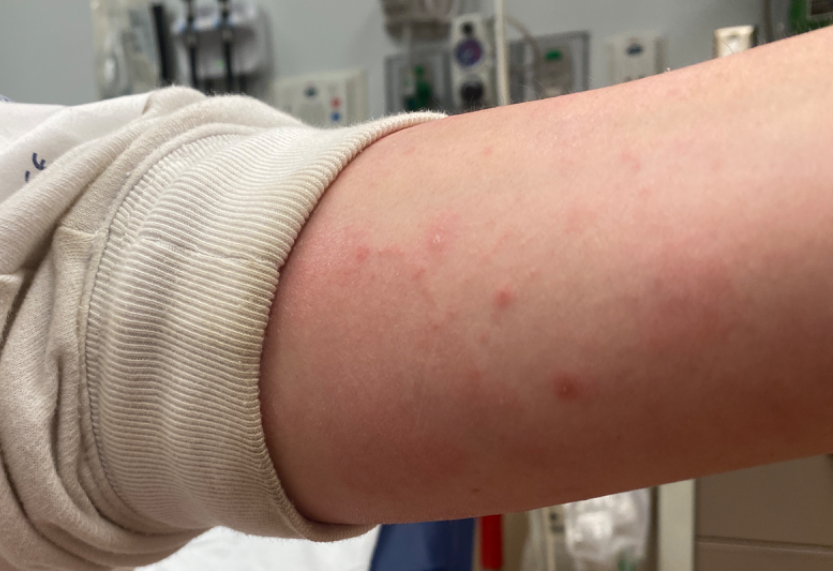Diagnostic features were not clearly distinguishable in this photograph.
The lesion involves the leg, front of the torso and arm.
The patient considered this a rash.
Texture is reported as rough or flaky.
An image taken at an angle.
Symptoms reported: itching and bothersome appearance.
The patient also reports shortness of breath and chills.